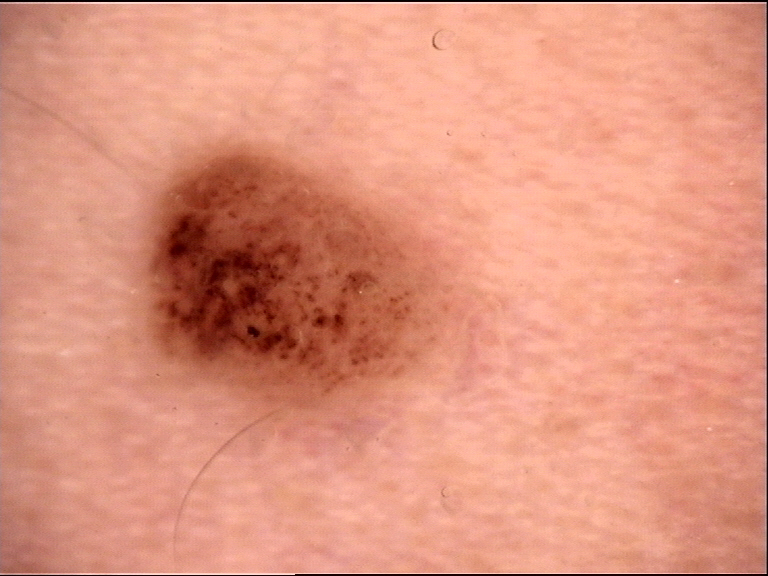Summary: A dermoscopic image of a skin lesion. This is a banal lesion. Impression: The diagnosis was a compound nevus.